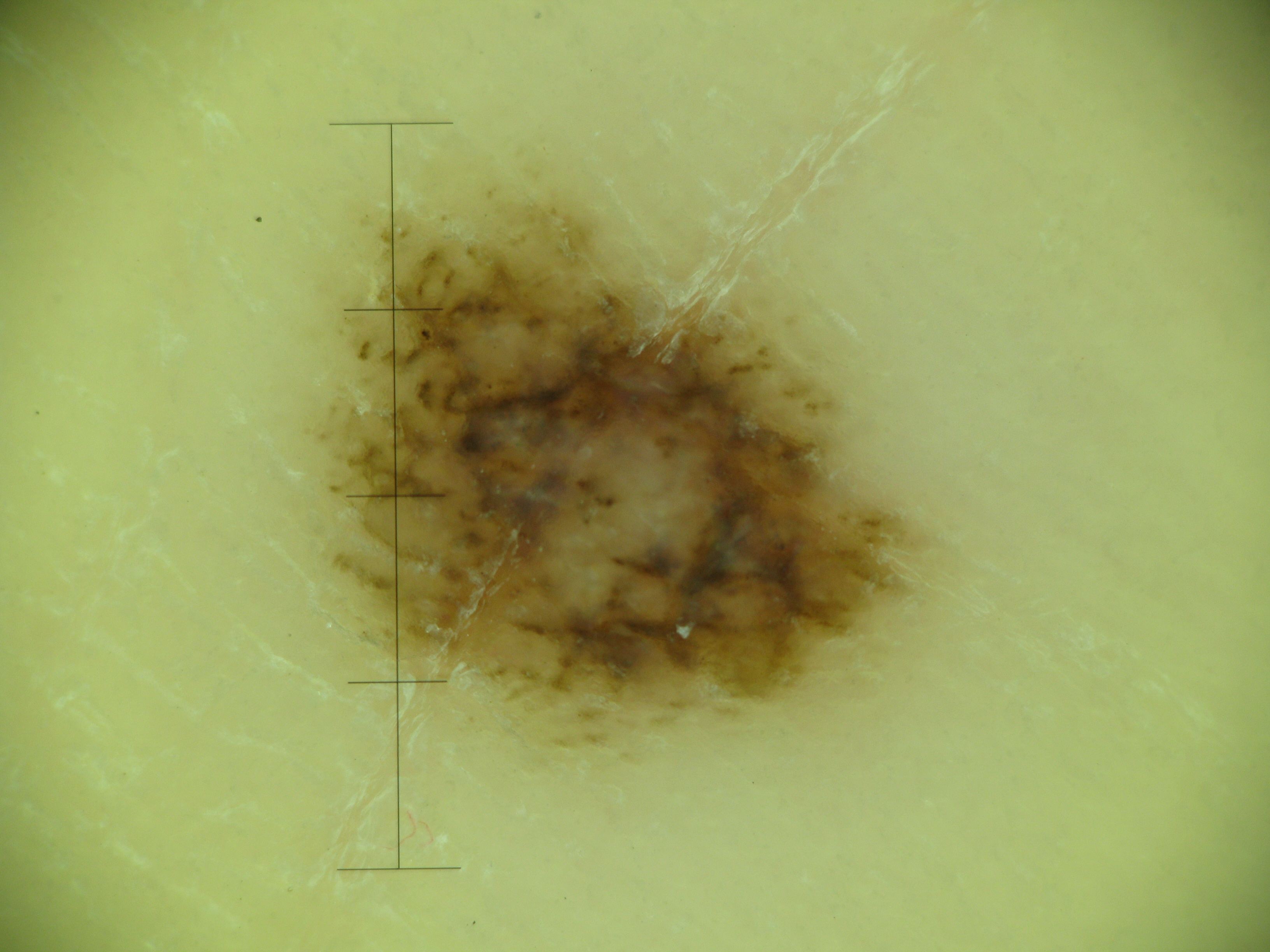Confirmed on histopathology as an acral lentiginous melanoma.